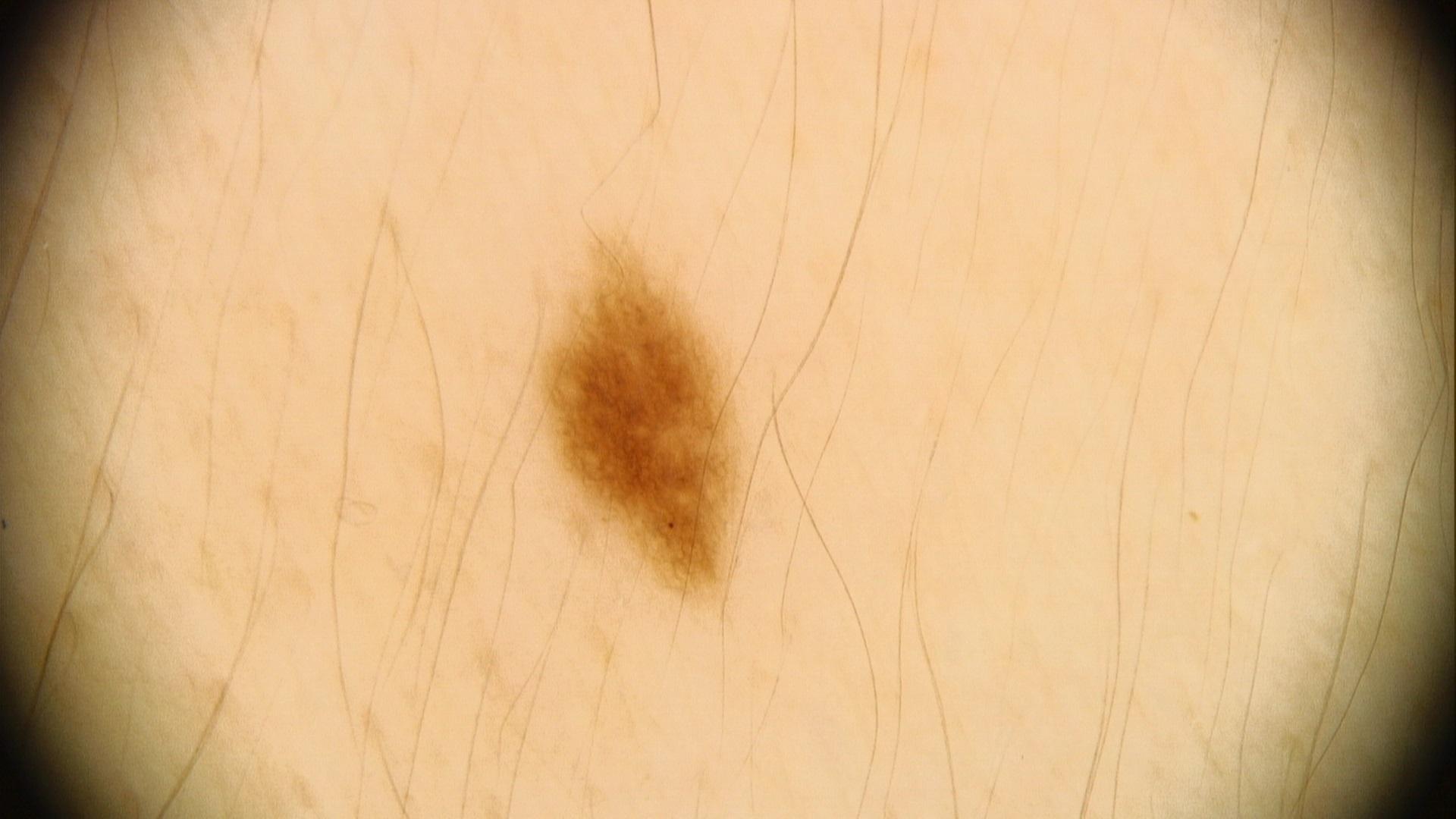The patient is Fitzpatrick phototype III.
Per the chart, a first-degree relative with melanoma.
A female patient in their 20s.
The lesion is located on the trunk.
Consistent with a benign, melanocytic lesion — a nevus.